A skin lesion imaged with a dermatoscope: 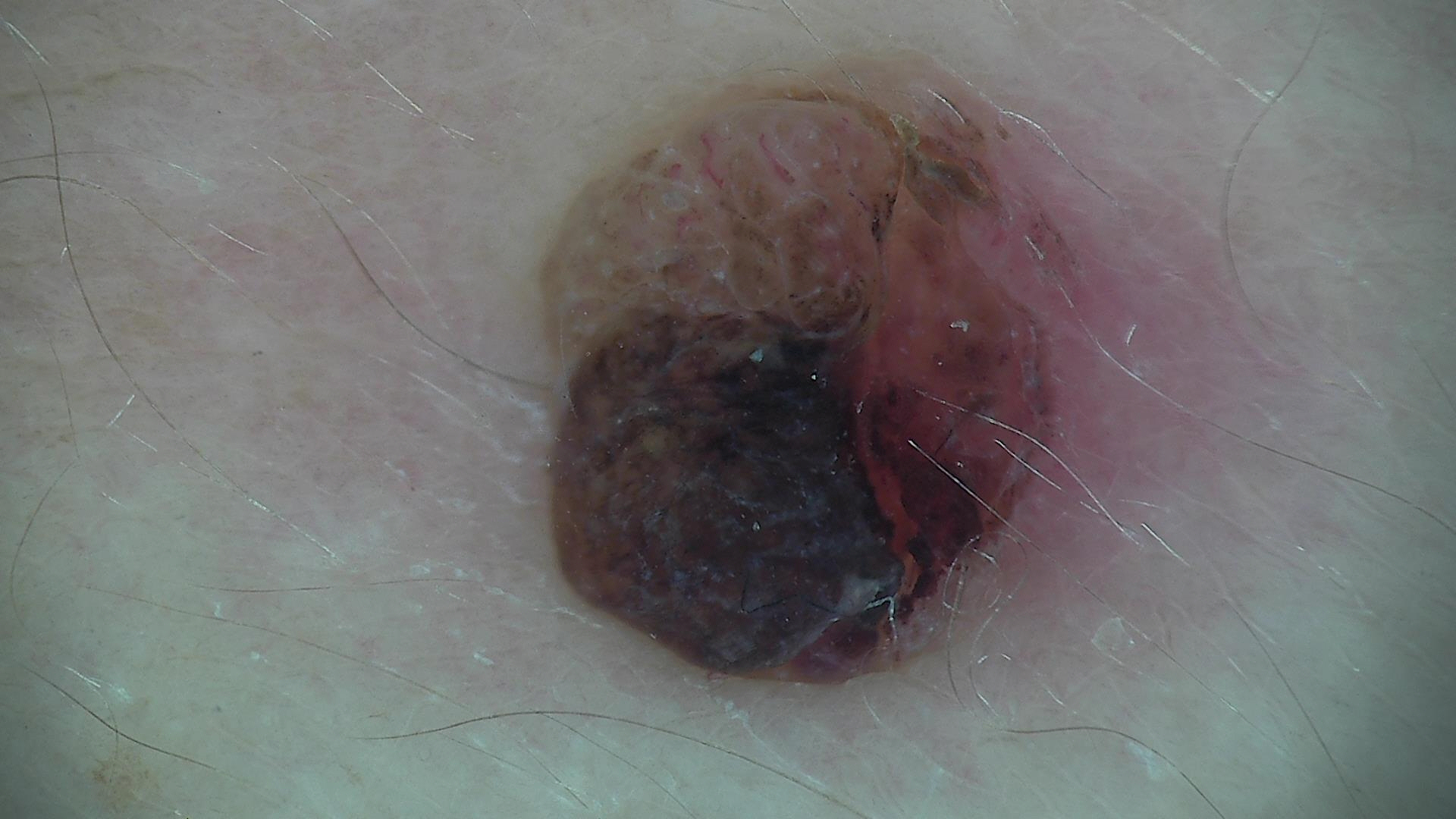Consistent with a banal lesion — a dermal nevus.